A dermoscopic image of a skin lesion:
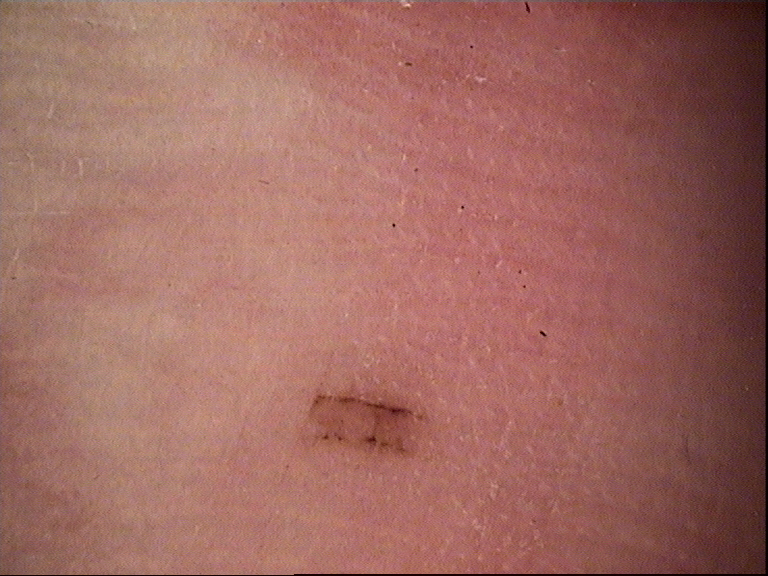Labeled as a benign lesion — an acral dysplastic junctional nevus.